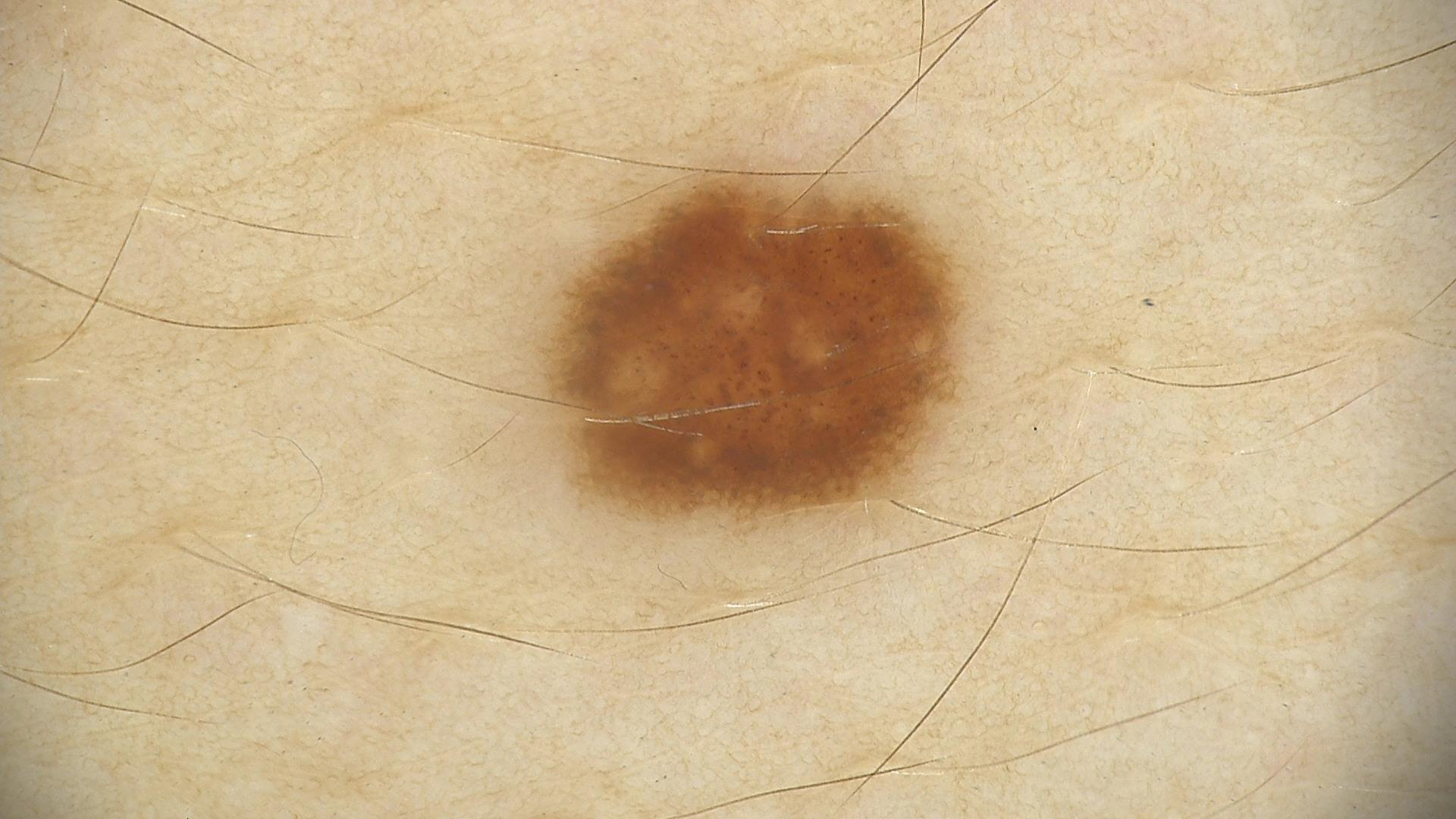label: dysplastic junctional nevus (expert consensus)